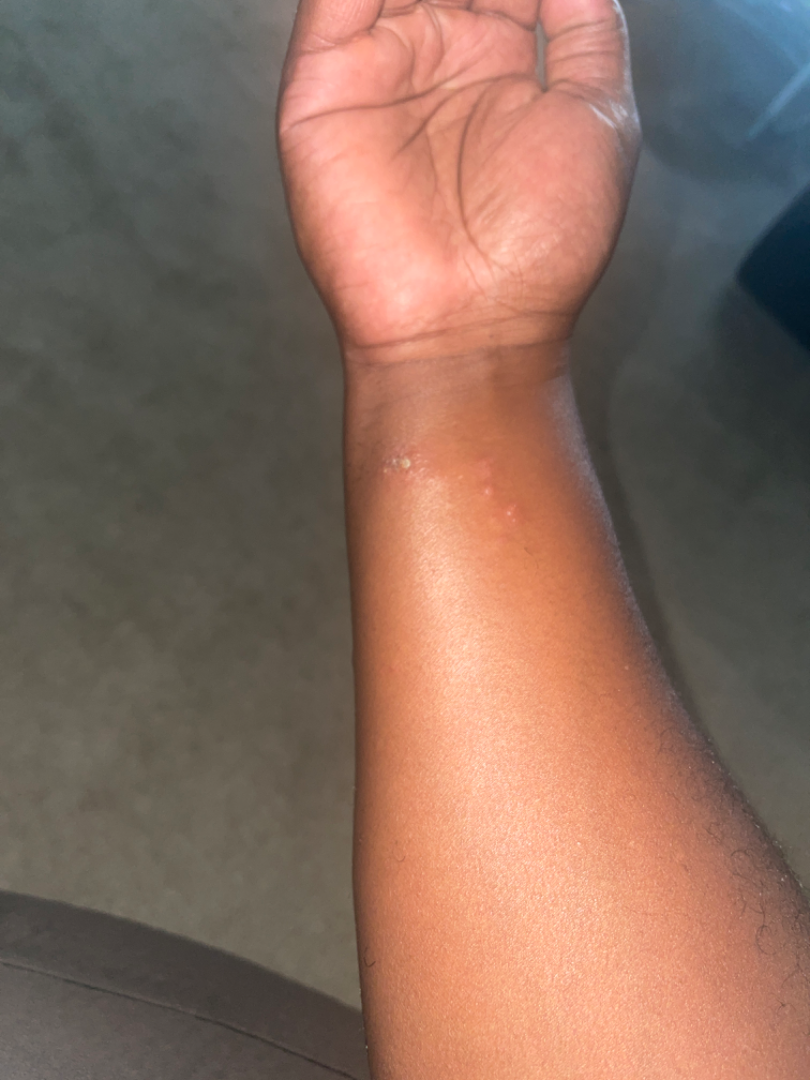{
  "shot_type": "at a distance",
  "patient": "male, age 40–49",
  "differential": {
    "tied_lead": [
      "Scabies",
      "Molluscum Contagiosum"
    ],
    "unlikely": [
      "Perforating dermatosis"
    ]
  }
}